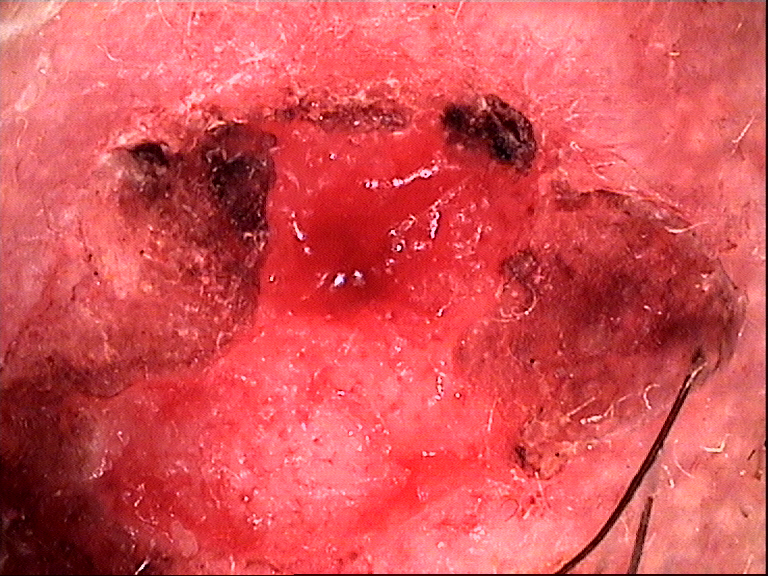diagnostic label = squamous cell carcinoma (biopsy-proven).